A dermoscopic image of a skin lesion · a female patient aged approximately 20 — 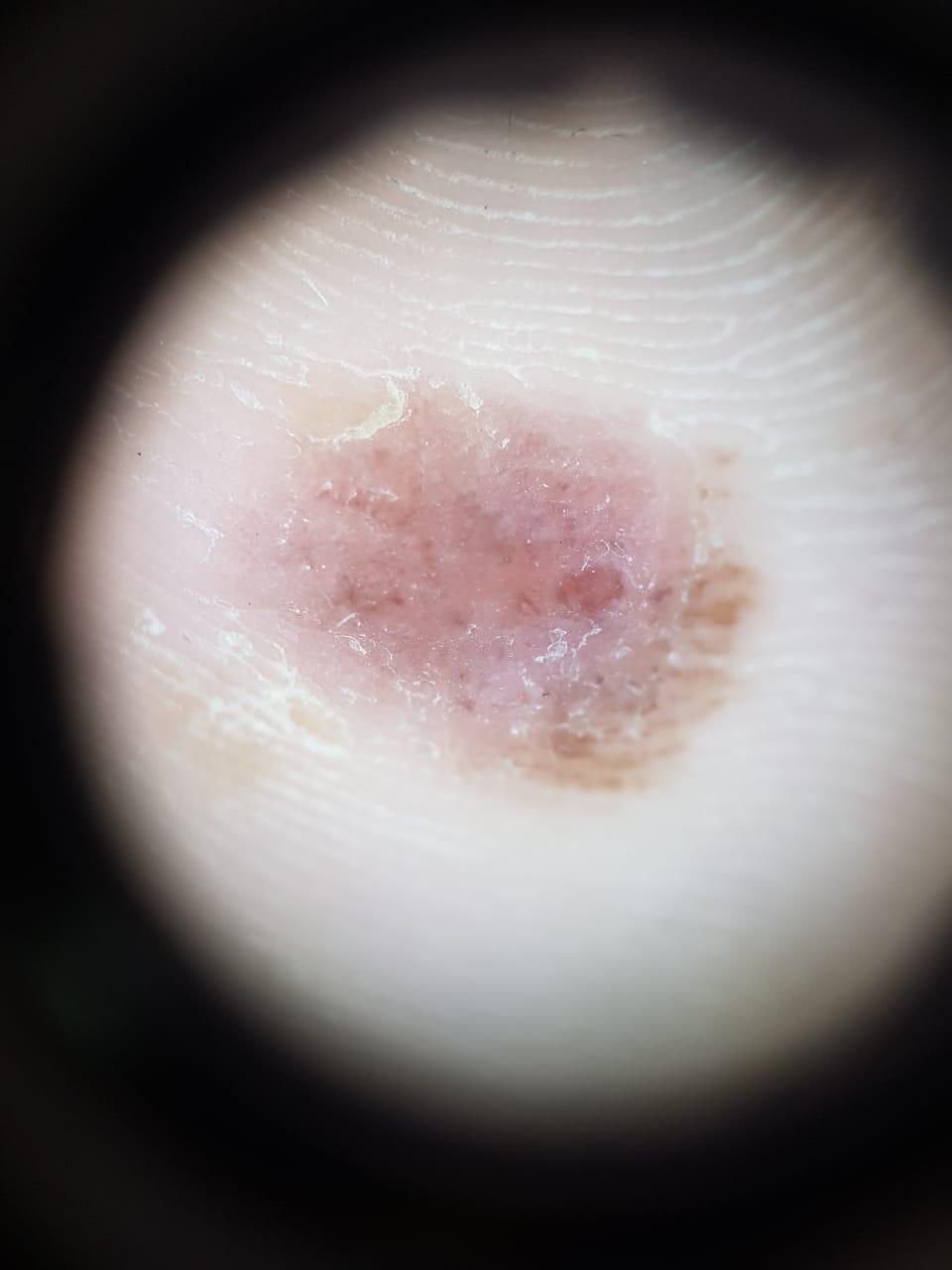Q: Where on the body is the lesion?
A: an acral site (palms or soles)
Q: What is the diagnosis?
A: Nevus (biopsy-proven)